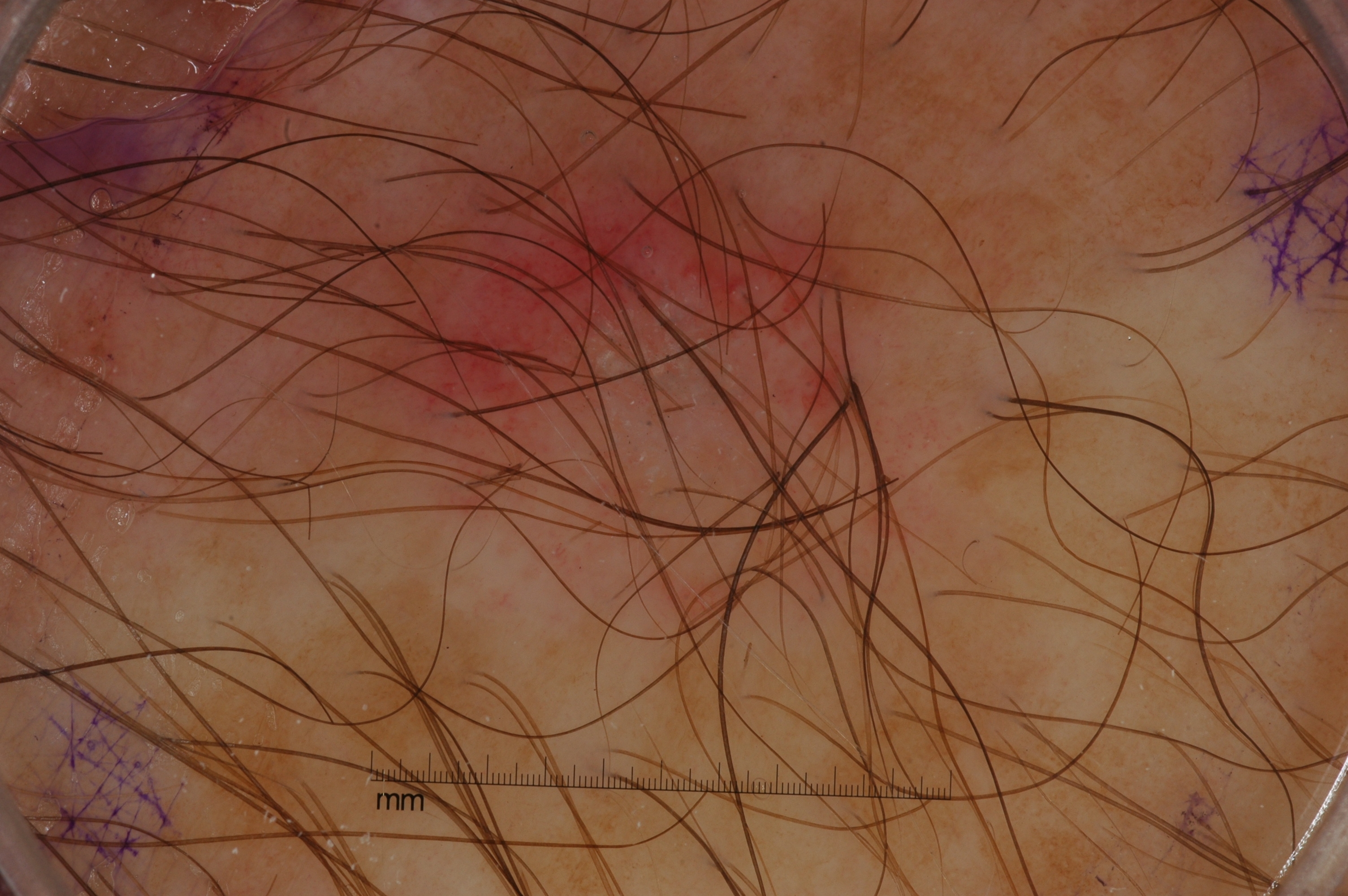  image:
    modality: dermoscopy
  patient:
    sex: male
    age_approx: 60
  lesion_location:
    bbox_xyxy:
      - 283
      - 66
      - 1005
      - 742
  dermoscopic_features:
    present: []
    absent:
      - negative network
      - streaks
      - milia-like cysts
      - pigment network
  diagnosis:
    name: seborrheic keratosis
    malignancy: benign
    lineage: keratinocytic
    provenance: clinical